Dermoscopy of a skin lesion: 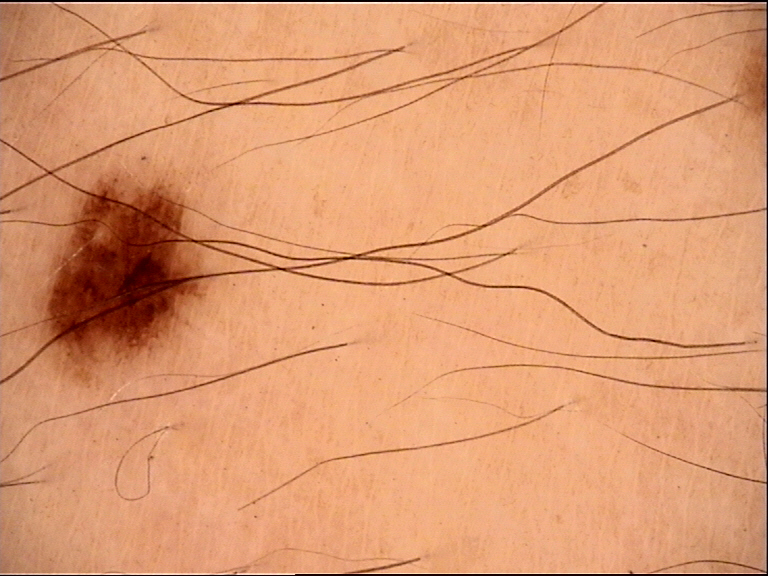Findings: The architecture is that of a banal lesion. Impression: Consistent with a junctional nevus.